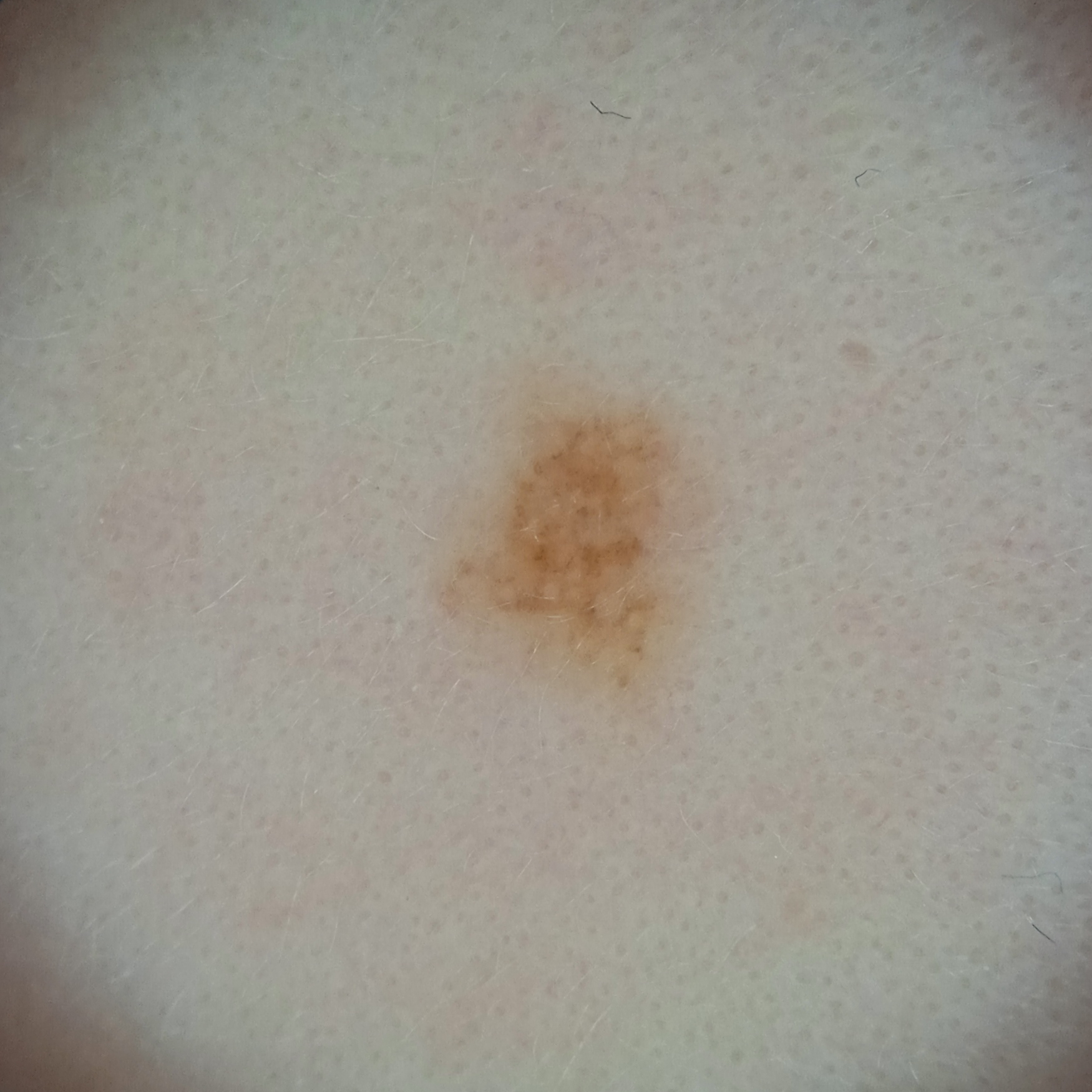A female subject 15 years of age. Few moles overall by the patient's own estimate. The patient says their skin reddens with sun exposure. A dermatoscopic image of a skin lesion. Collected as part of a research study, without a referral diagnosis. The lesion is located on the face. The lesion was assessed as a melanocytic nevus.